Dermoscopy of a skin lesion · a female patient, in their mid-40s: 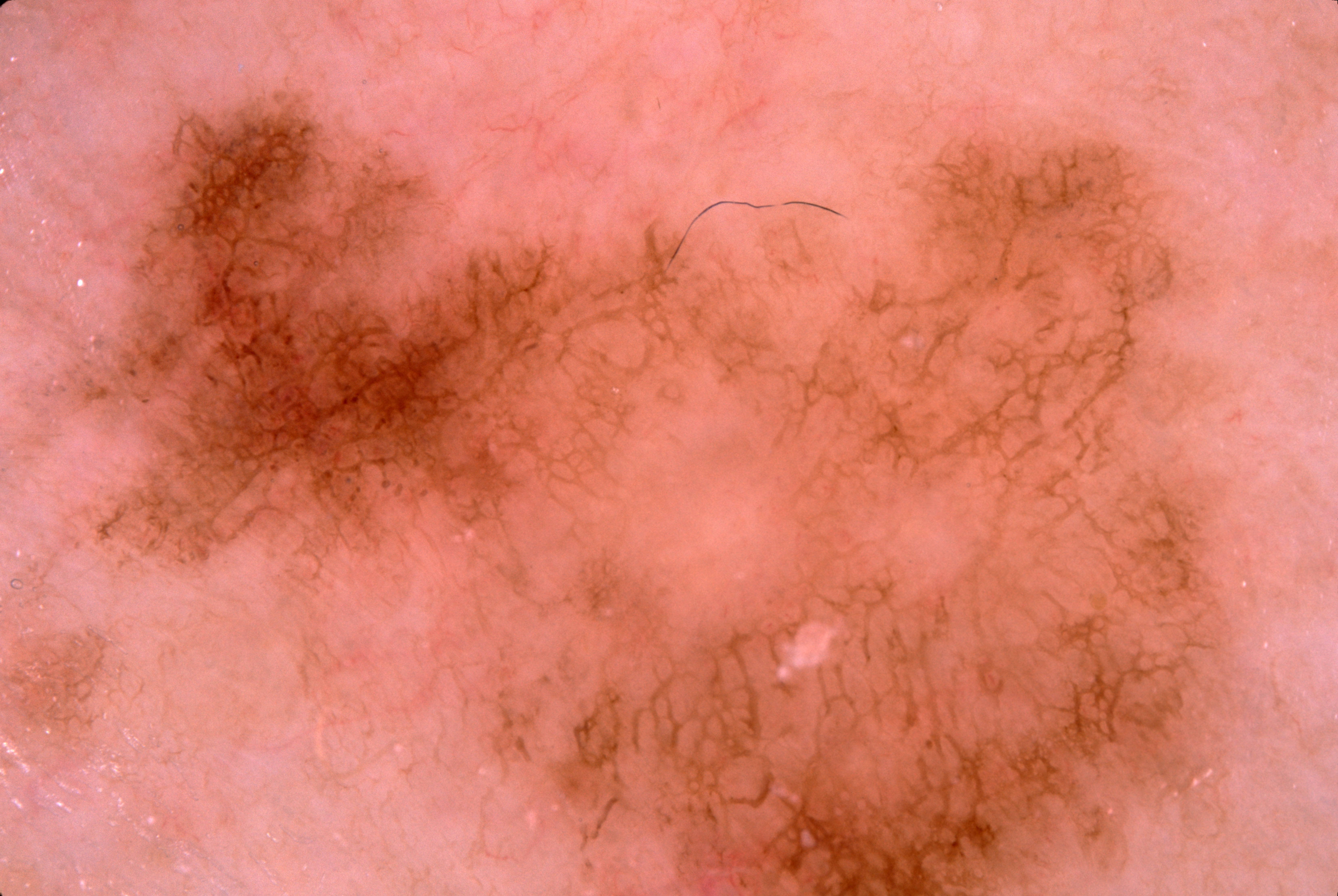features=pigment network | lesion margin=extends past the field edge | location=(84, 70, 1254, 895) | diagnosis=a melanocytic nevus.